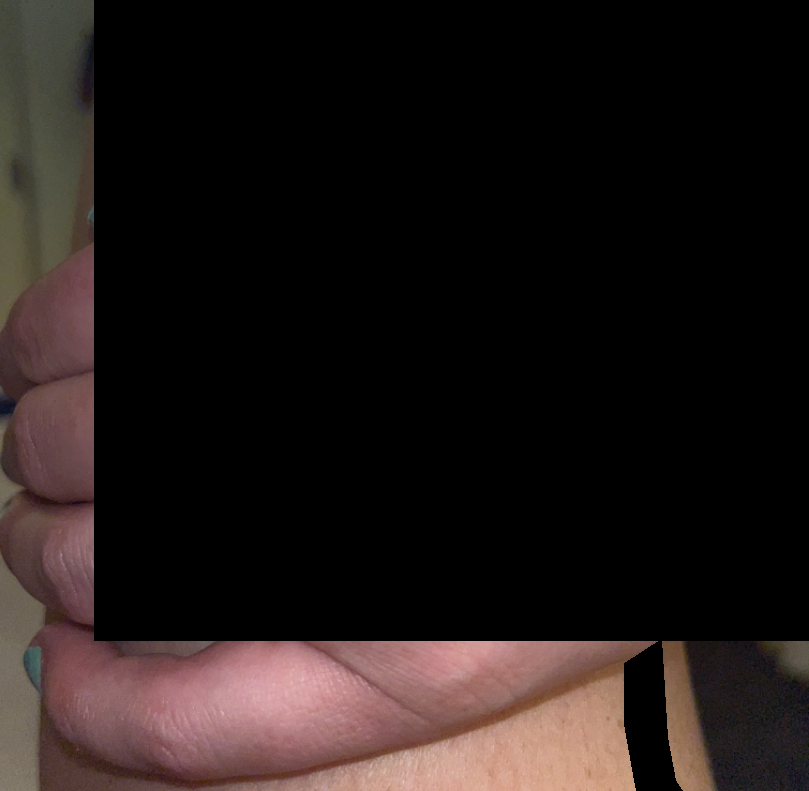shot_type: close-up
body_site: back of the hand
patient: female, age 30–39
differential:
  leading:
    - Allergic Contact Dermatitis
  considered:
    - Eczema
    - Irritant Contact Dermatitis